A dermatoscopic image of a skin lesion.
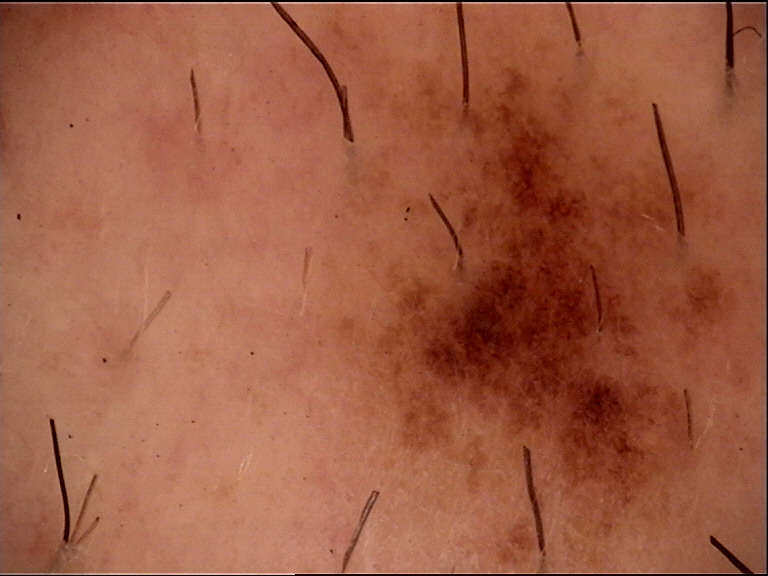label: dysplastic junctional nevus (expert consensus).